A dermoscopic image of a skin lesion · the patient describes having a moderate number of moles · a female patient 59 years of age:
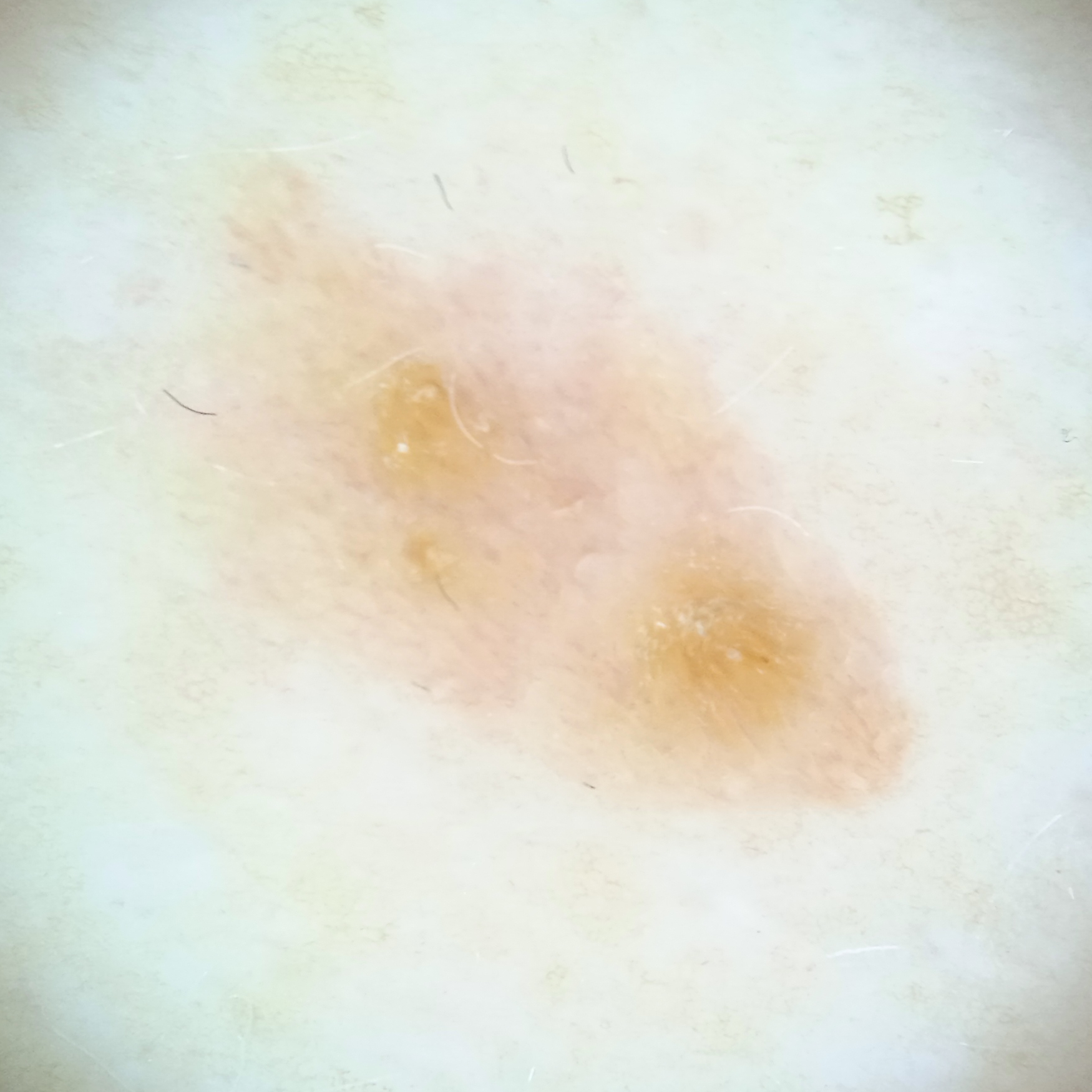Q: What is the anatomic site?
A: the torso
Q: Lesion size?
A: 9.1 mm
Q: What was the diagnosis?
A: seborrheic keratosis (dermatologist consensus)